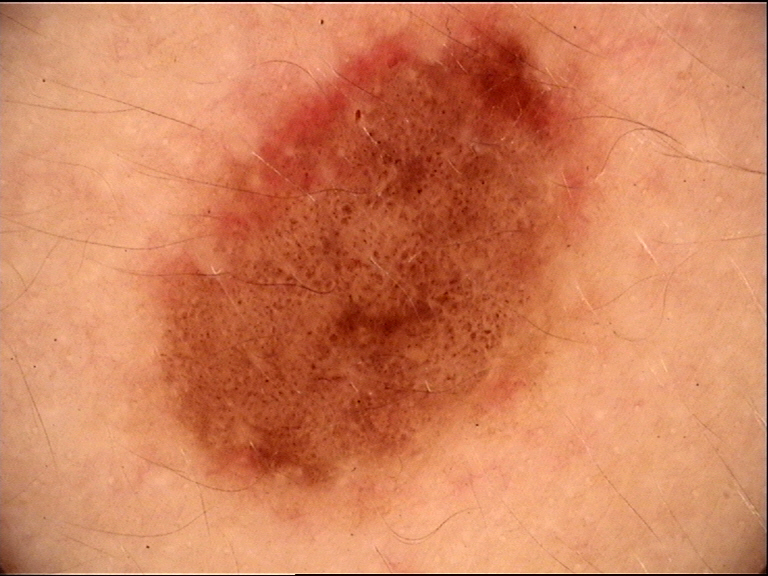The diagnostic label was a benign lesion — a dysplastic junctional nevus.